Located on the back of the hand and palm · skin tone: Fitzpatrick phototype IV; non-clinician graders estimated Monk Skin Tone 8 (US pool) or 5 (India pool) · the patient described the issue as a rash · the patient notes the lesion is fluid-filled · the patient notes the condition has been present for one to four weeks · no relevant systemic symptoms · close-up view · symptoms reported: bothersome appearance, bleeding, pain, burning, enlargement, darkening and itching:
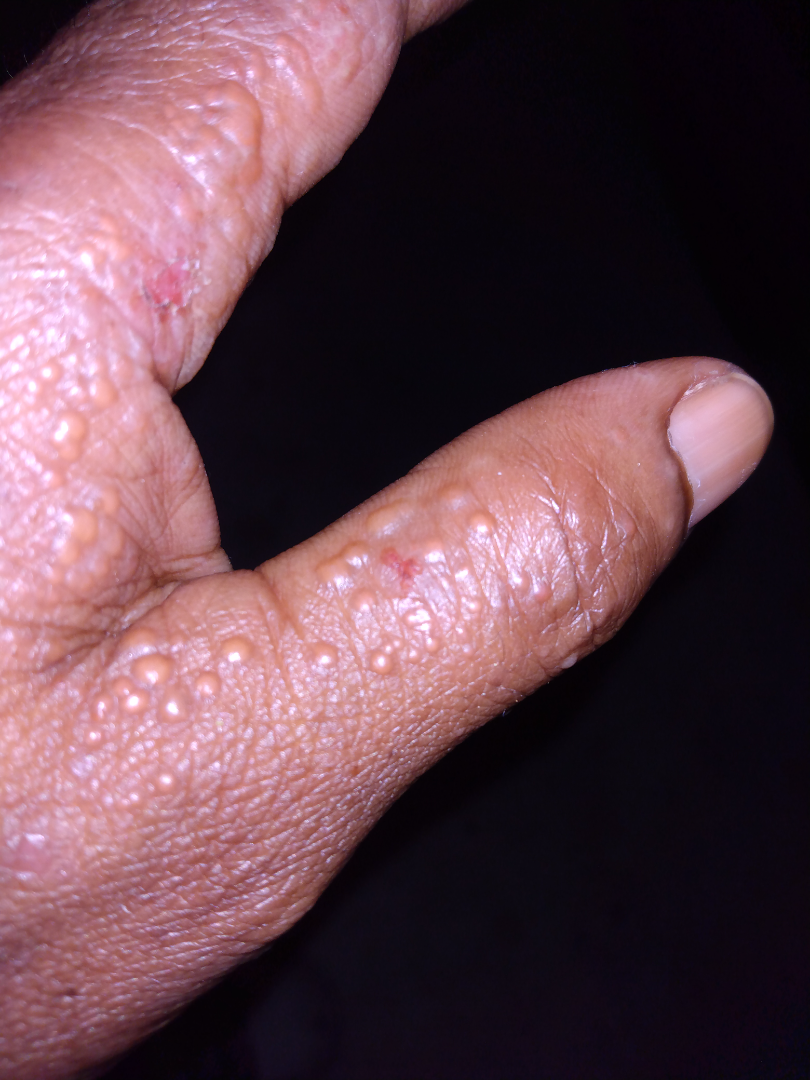Assessment:
On photographic review: the primary impression is Eczema.